A male subject roughly 65 years of age. A dermatoscopic image of a skin lesion.
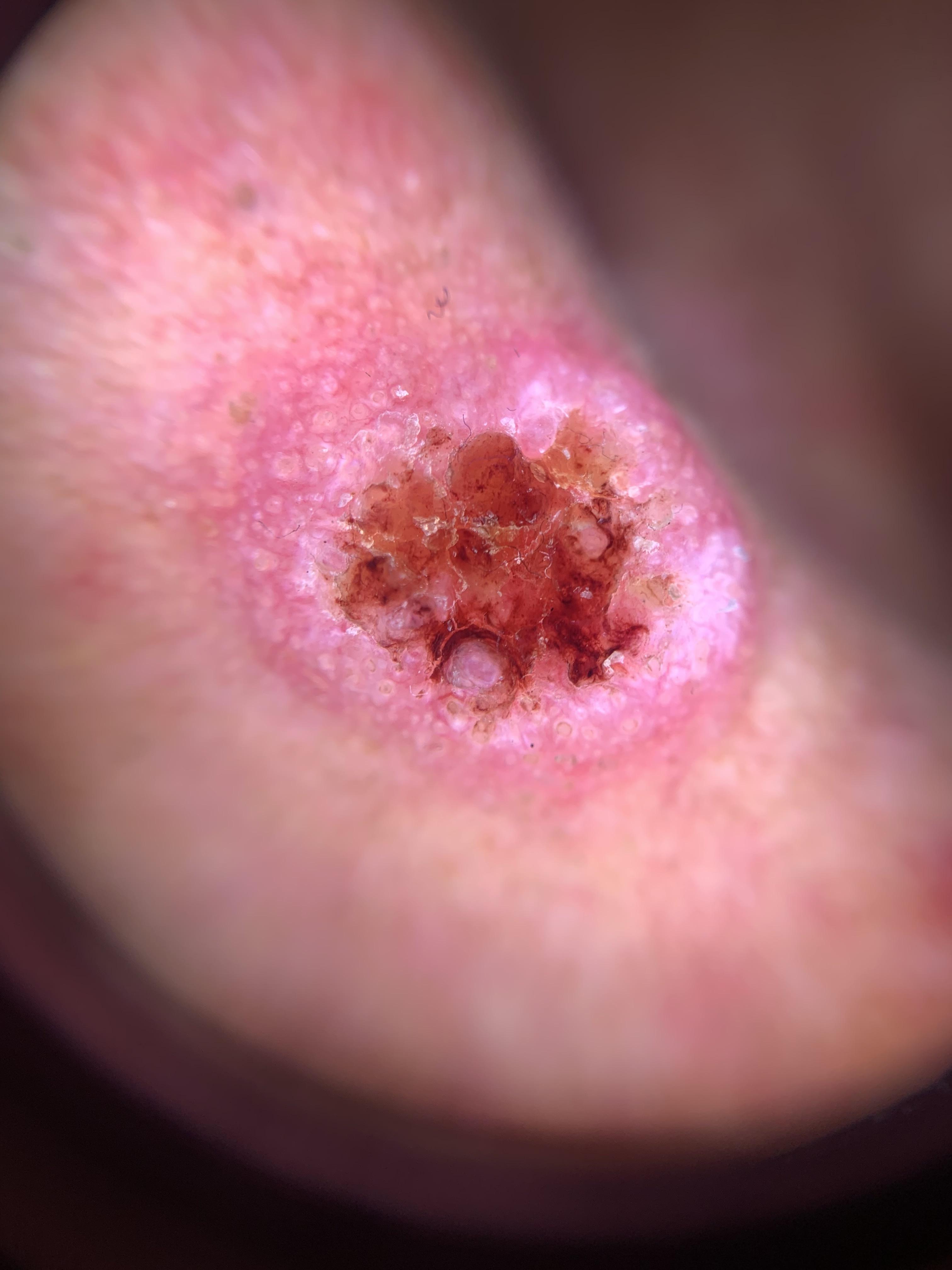The lesion involves the head or neck.
Histopathological examination showed a squamous cell carcinoma.